A dermatoscopic image of a skin lesion:
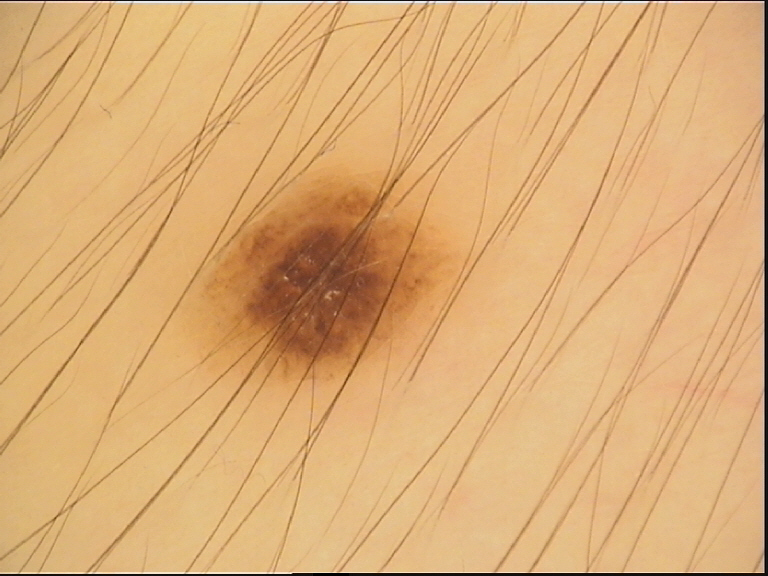diagnosis = dysplastic junctional nevus (expert consensus).